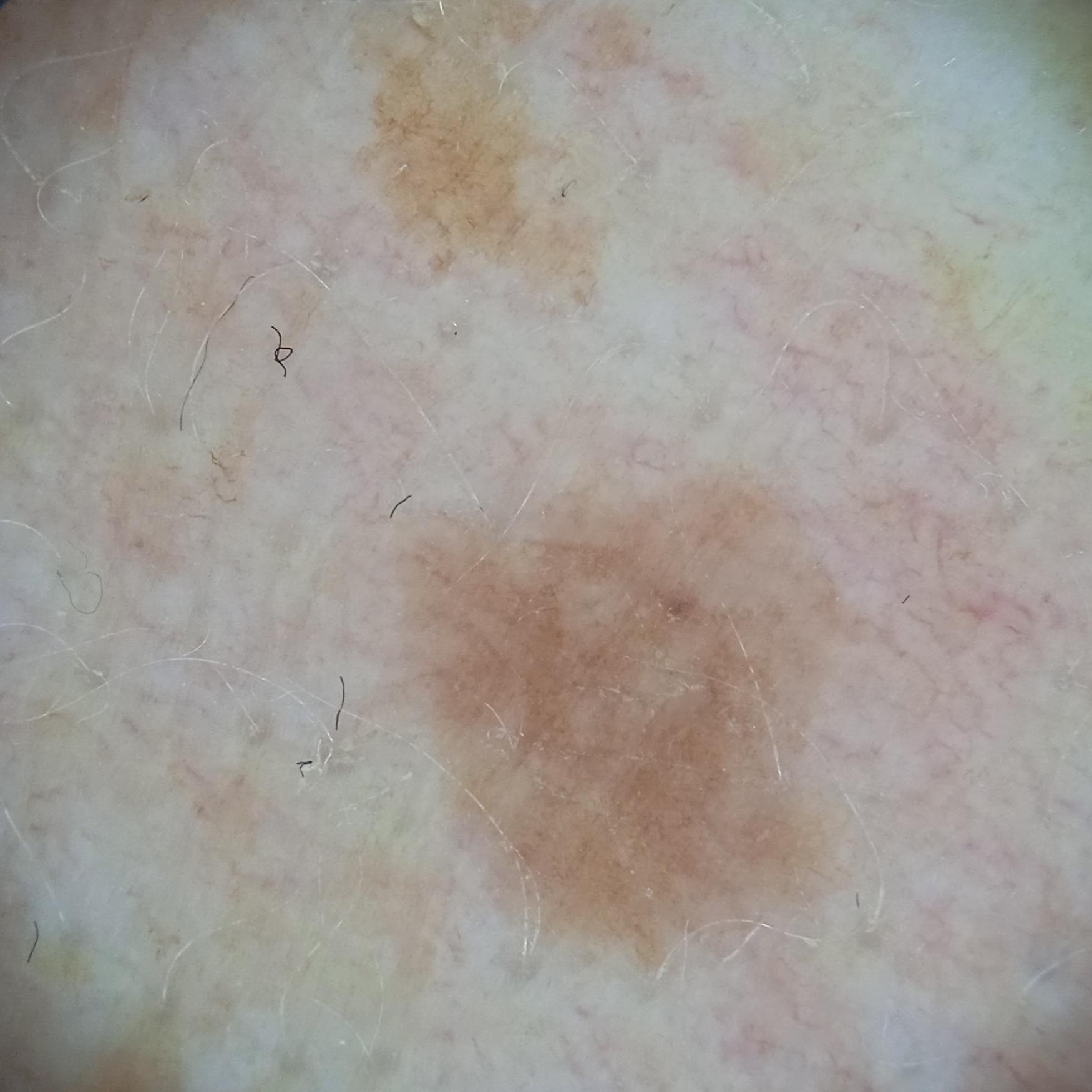A female patient aged 59. Acquired for a research image collection, with no referral diagnosis. The lesion is located on an arm. The lesion measures approximately 6.5 mm. The four-dermatologist consensus diagnosis was a melanocytic nevus; the reviewers were moderately confident.